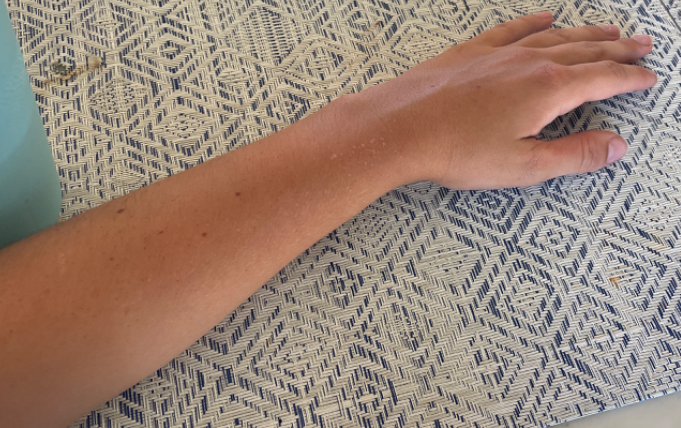The condition could not be reliably identified from the image. An image taken at a distance.